A skin lesion imaged with a dermatoscope:
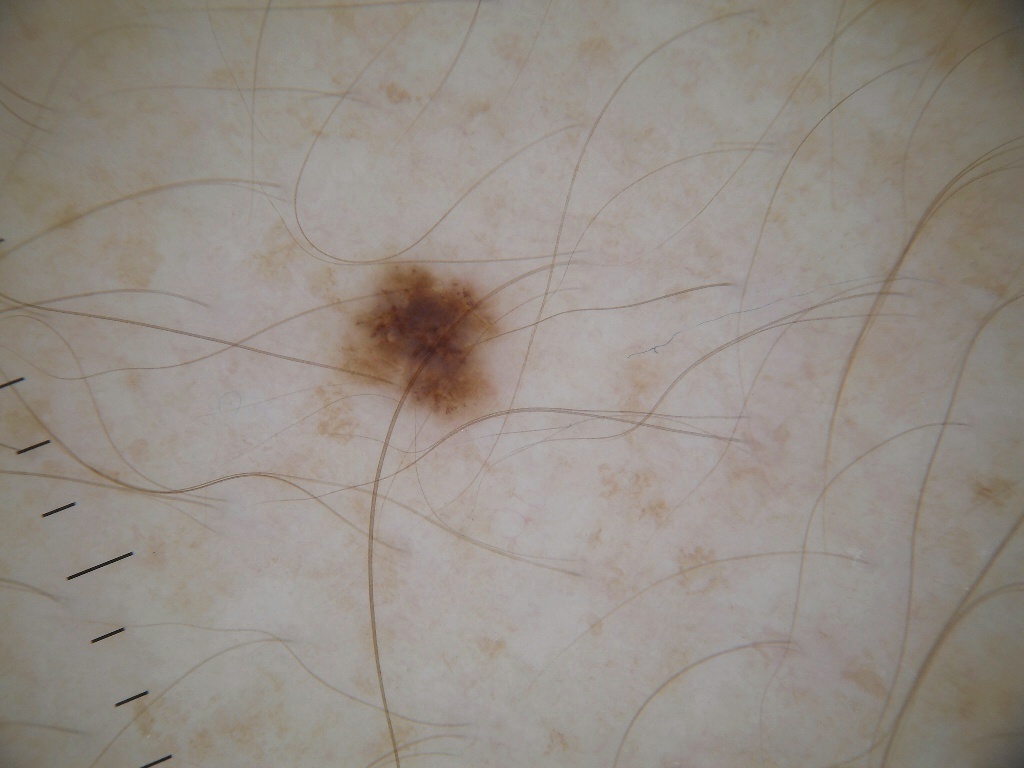{"lesion_location": {"bbox_xyxy": [323, 246, 517, 438]}, "diagnosis": {"name": "melanocytic nevus", "malignancy": "benign", "lineage": "melanocytic", "provenance": "clinical"}}